A dermoscopic image of a skin lesion: 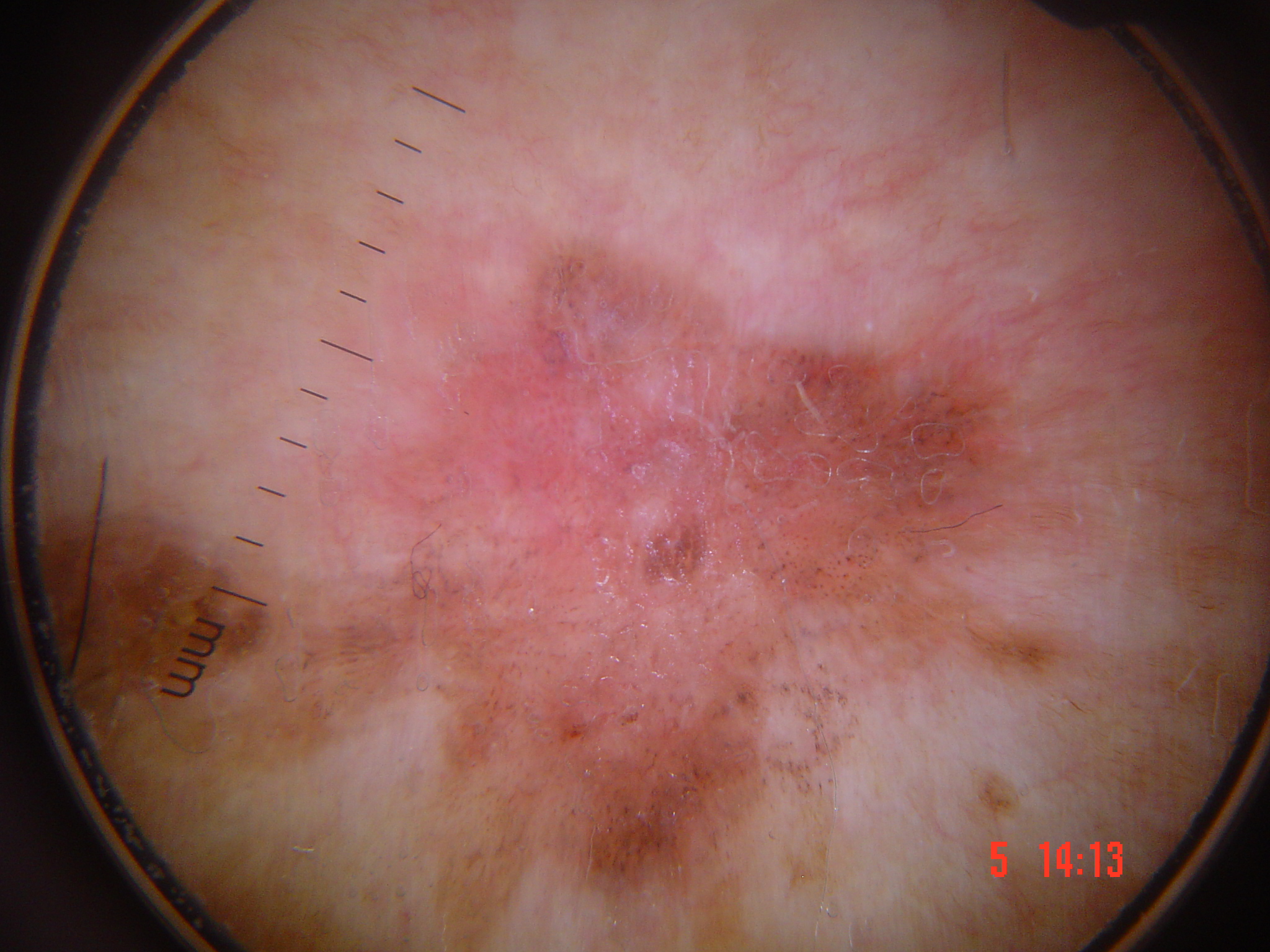The architecture is that of a keratinocytic lesion.
Histopathology confirmed Bowen's disease.